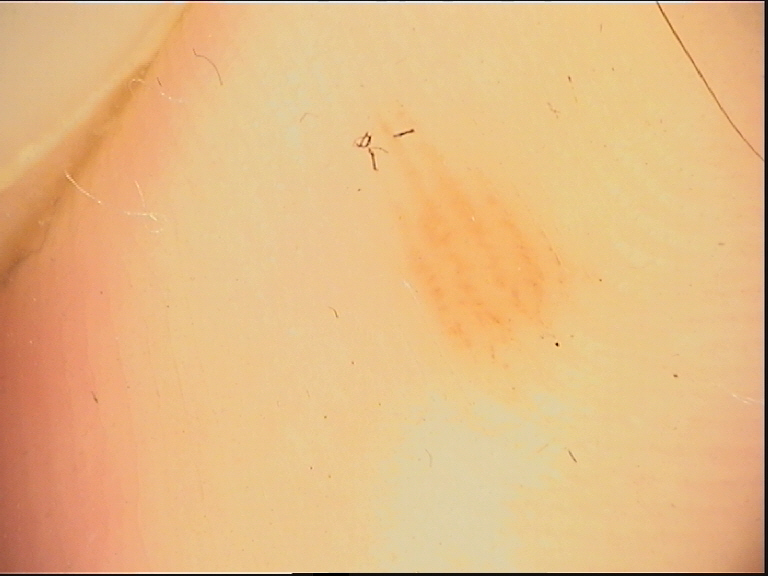Conclusion: The diagnostic label was an acral junctional nevus.